A dermatoscopic image of a skin lesion.
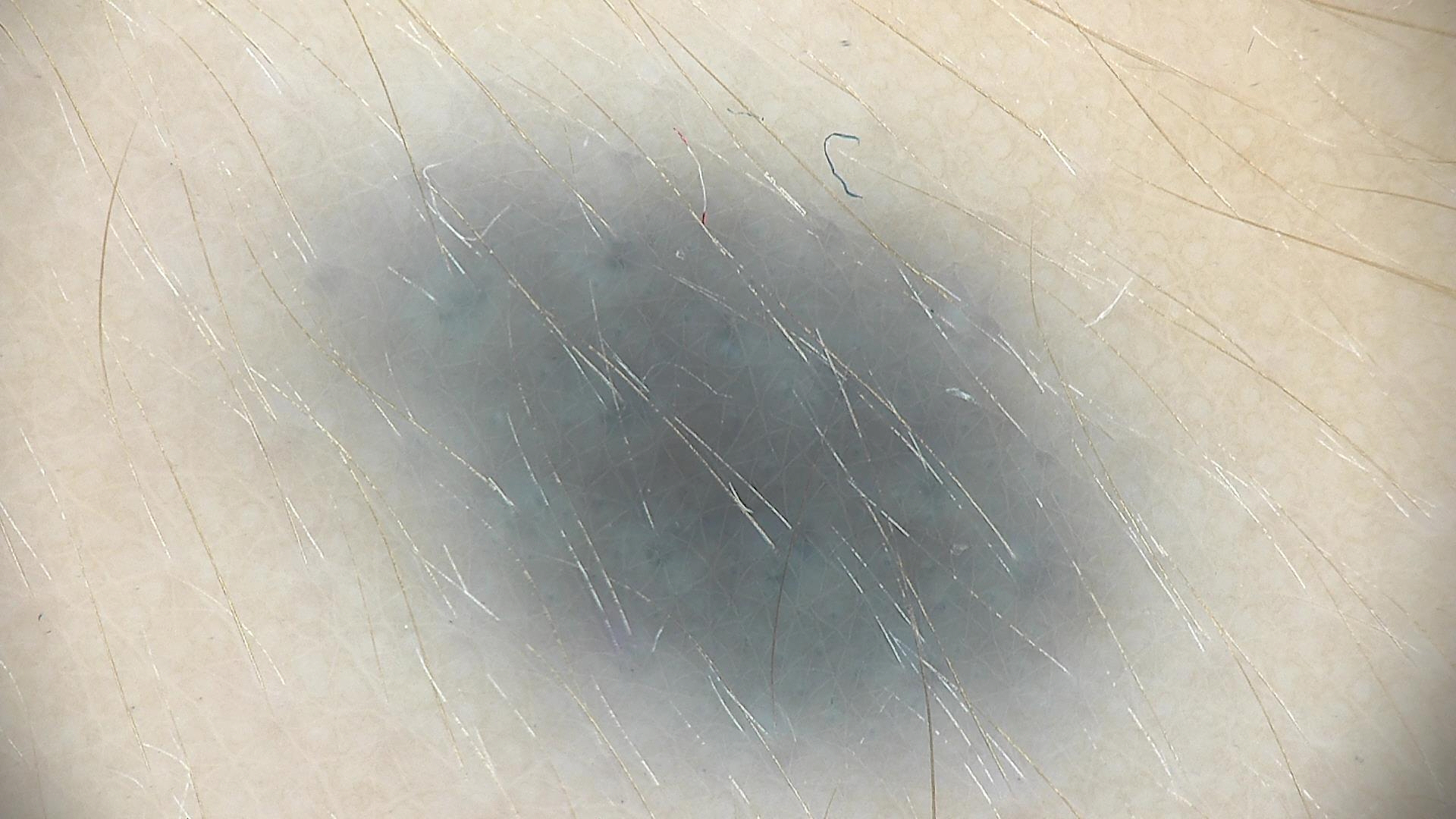Conclusion:
The diagnostic label was a banal lesion — a blue nevus.